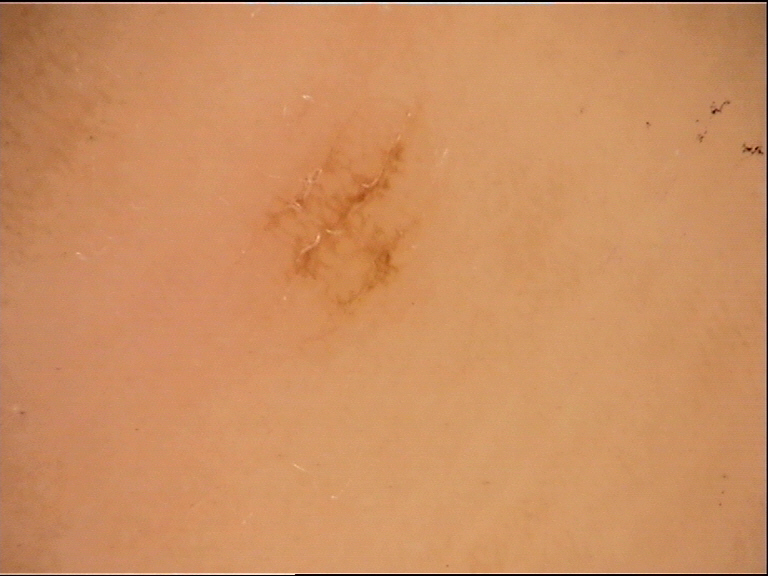Conclusion: The diagnostic label was a banal lesion — an acral junctional nevus.